A dermatoscopic image of a skin lesion; referred for assessment of suspected basal cell carcinoma; a male patient 60 years of age — 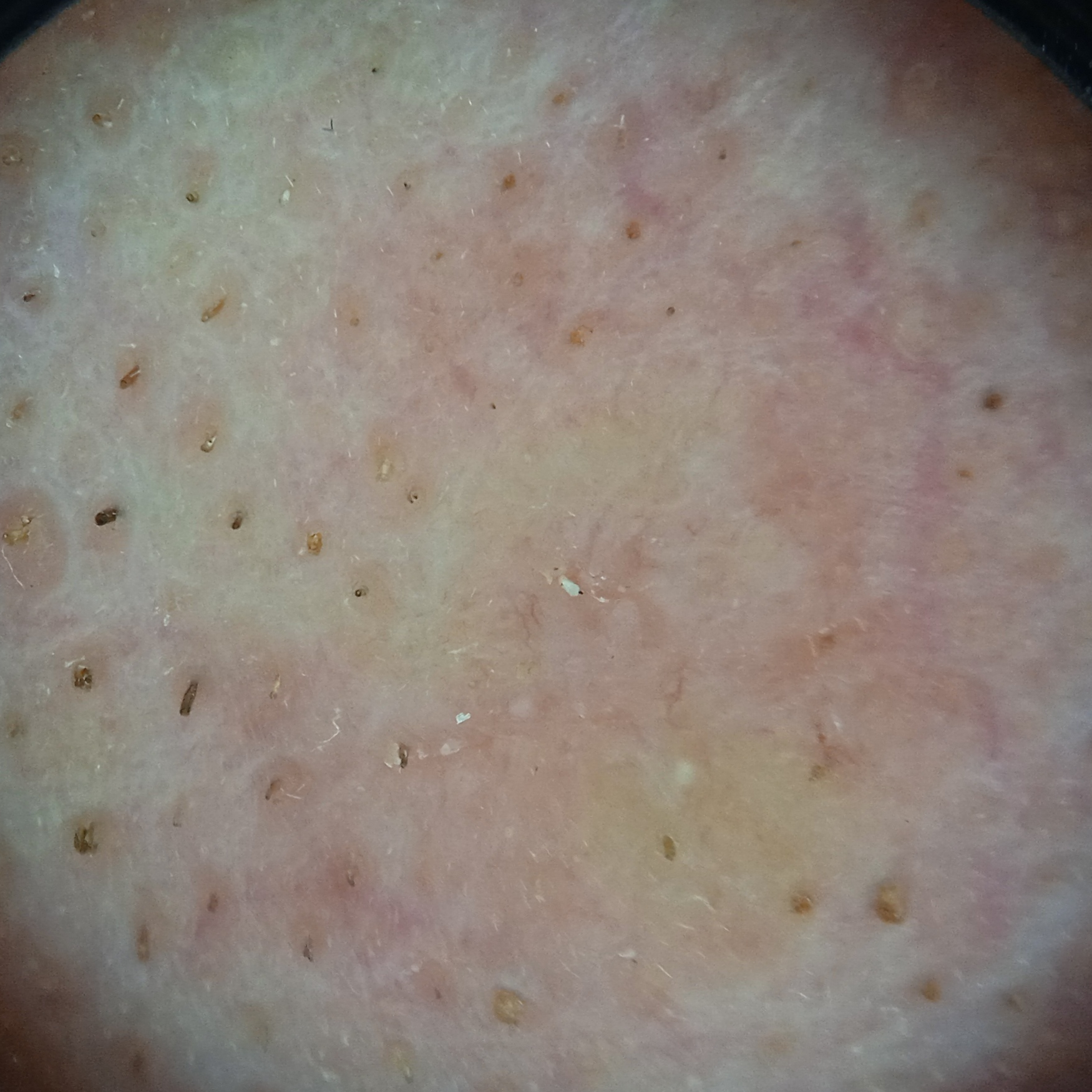The lesion is located on the face. The lesion measures approximately 8.5 mm. Histopathology confirmed a basal cell carcinoma, following excision, with a measured thickness of 1.7 mm.